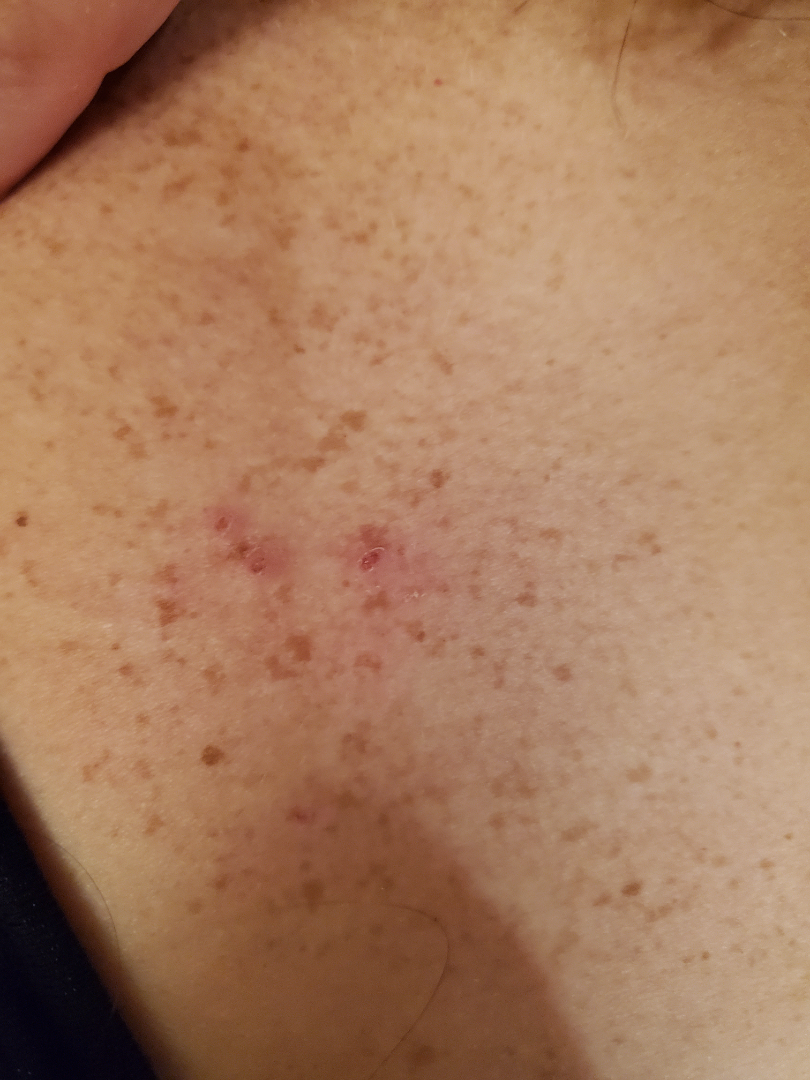Review:
The image was not sufficient for the reviewer to characterize the skin condition.
Patient information:
The photo was captured at an angle.